A skin lesion imaged with a dermatoscope, a female patient aged around 15 — 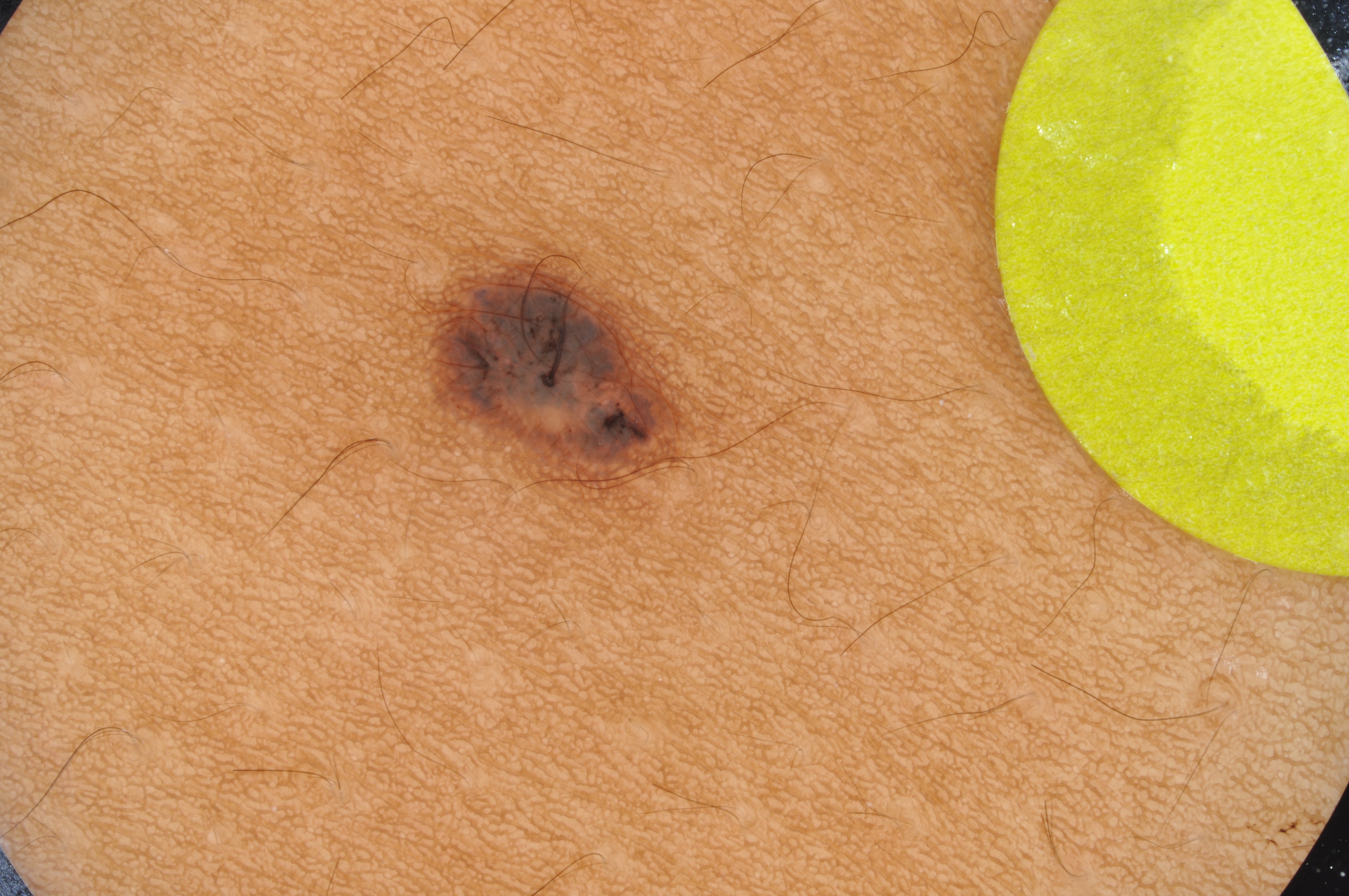A small lesion occupying a minor part of the field.
Dermoscopy demonstrates no streaks, milia-like cysts, pigment network, globules, or negative network.
With coordinates (x1, y1, x2, y2), the lesion spans [423, 245, 683, 494].
The clinical diagnosis was a melanocytic nevus, a benign lesion.